The photograph was taken at a distance; the leg, arm, top or side of the foot, front of the torso and head or neck are involved; the contributor is 50–59, female:
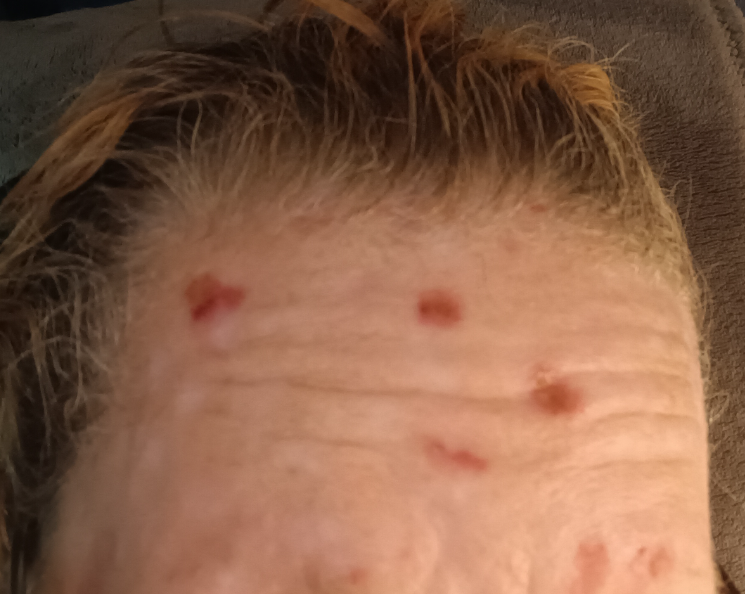On photographic review: Acne (leading); Inflicted skin lesions (considered); Impetigo (remote); Lichen Simplex Chronicus (remote); Herpes Zoster (remote).